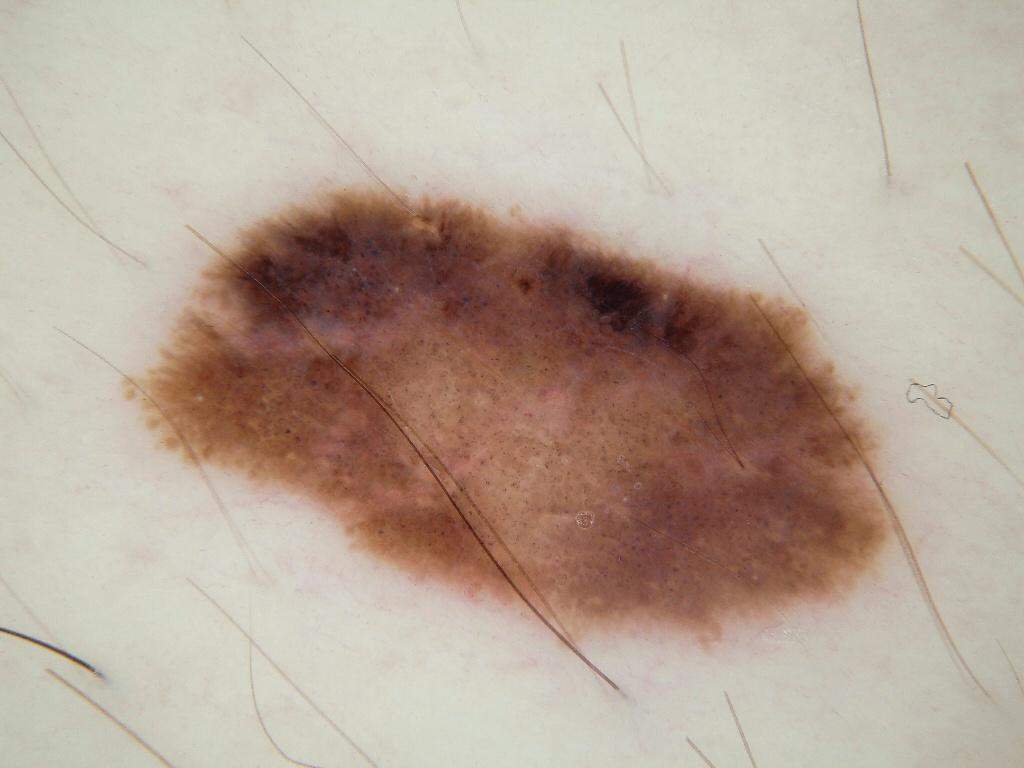A dermatoscopic image of a skin lesion.
A male patient aged 28 to 32.
In (x1, y1, x2, y2) order, the lesion occupies the region bbox(119, 179, 897, 660).
The lesion occupies roughly 32% of the field.
Dermoscopic review identifies globules, milia-like cysts, and streaks.
The clinical diagnosis was a melanocytic nevus, a benign skin lesion.